A dermatoscopic image of a skin lesion.
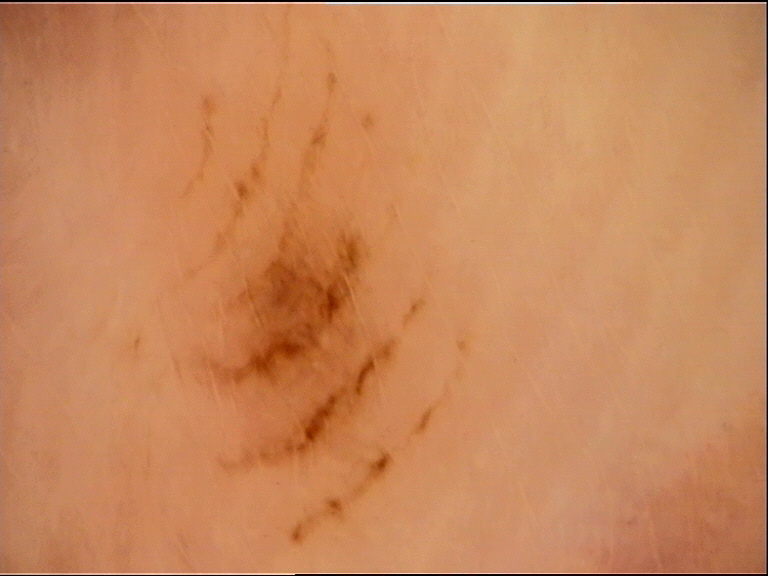<dermoscopy>
<diagnosis>
<name>acral junctional nevus</name>
<code>ajb</code>
<malignancy>benign</malignancy>
<super_class>melanocytic</super_class>
<confirmation>expert consensus</confirmation>
</diagnosis>
</dermoscopy>